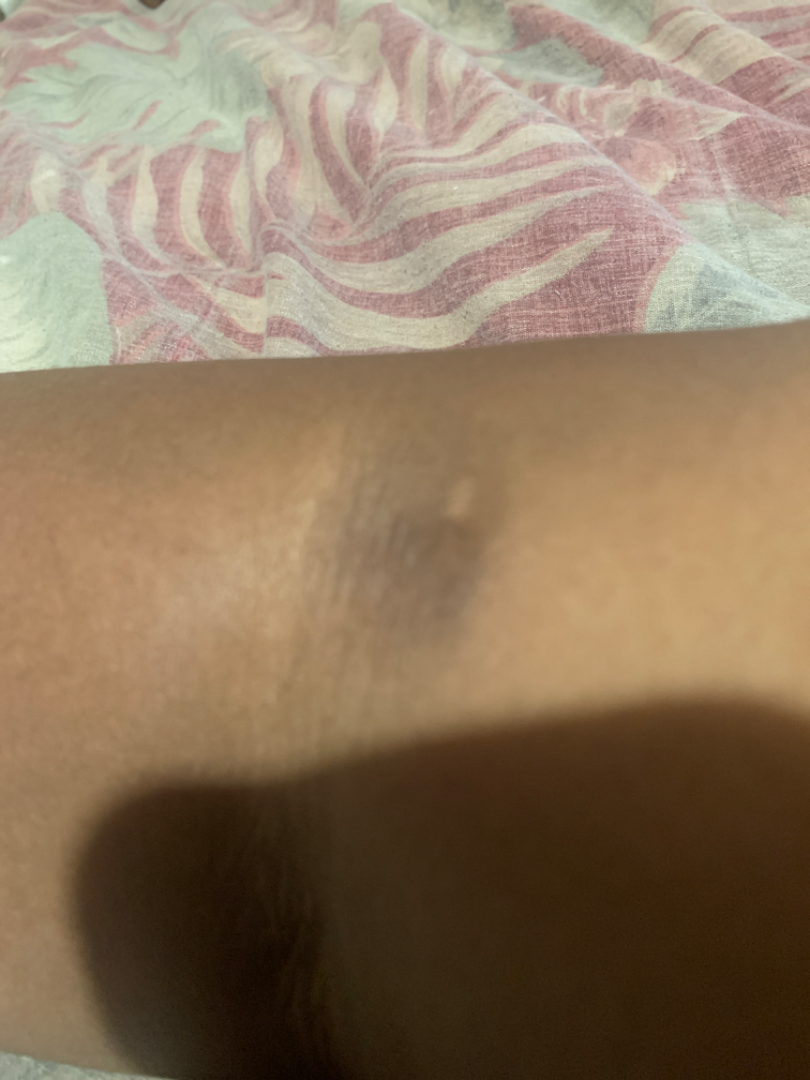assessment = not assessable | shot type = close-up | skin tone = FST V; non-clinician graders estimated MST 6 (US pool) or 4 (India pool).